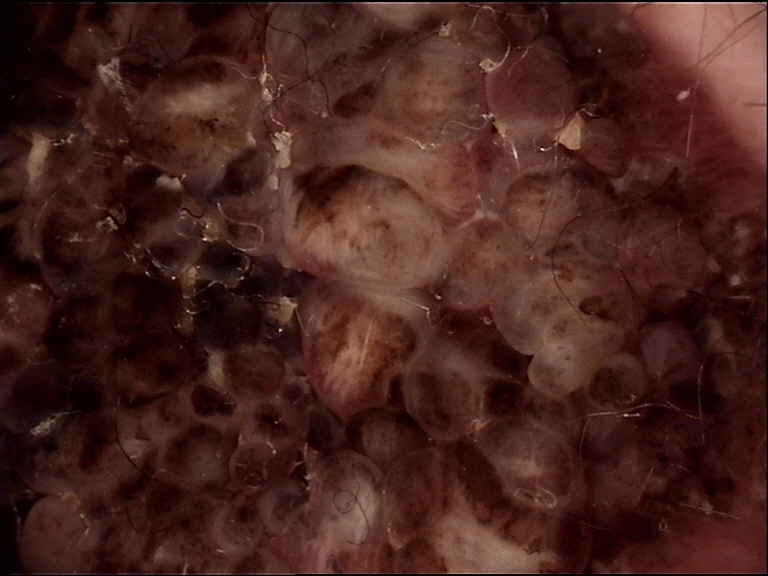A dermatoscopic image of a skin lesion.
Labeled as a banal lesion — a congenital compound nevus.